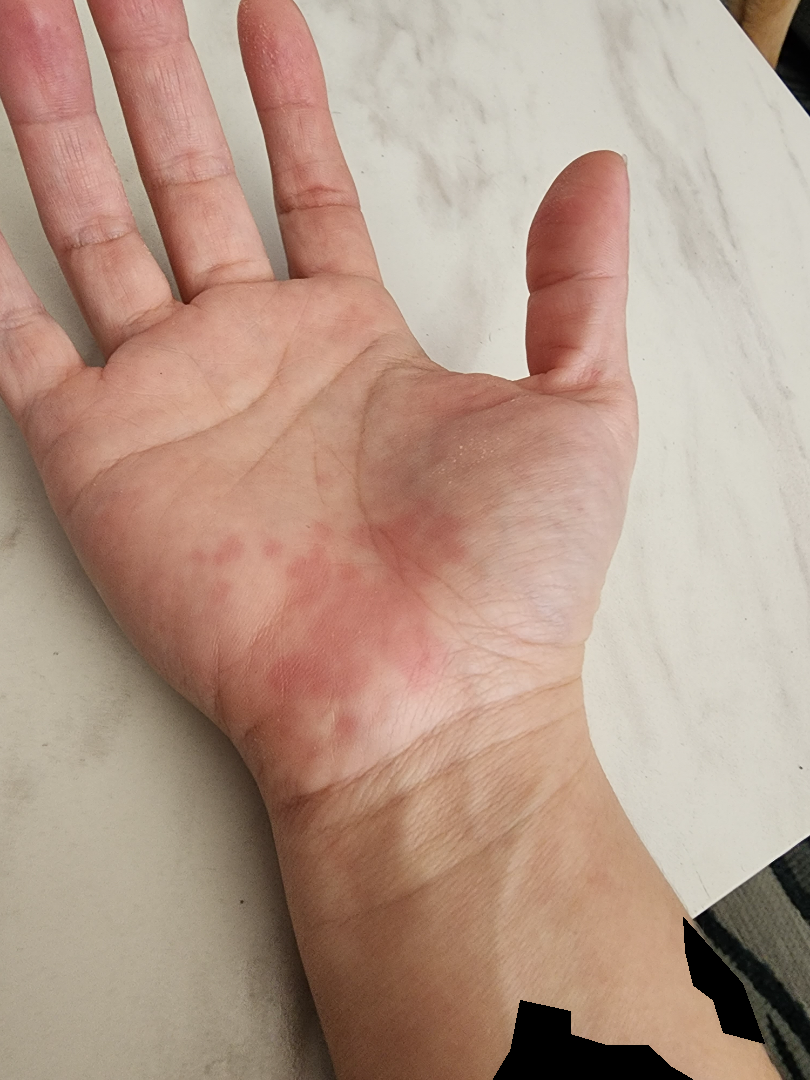photo taken = at an angle | location = palm | diagnostic considerations = Allergic Contact Dermatitis (favored); Psoriasis (considered); Insect Bite (considered).